The patient is skin type III. A clinical photograph showing a skin lesion. A male subject aged 34 — 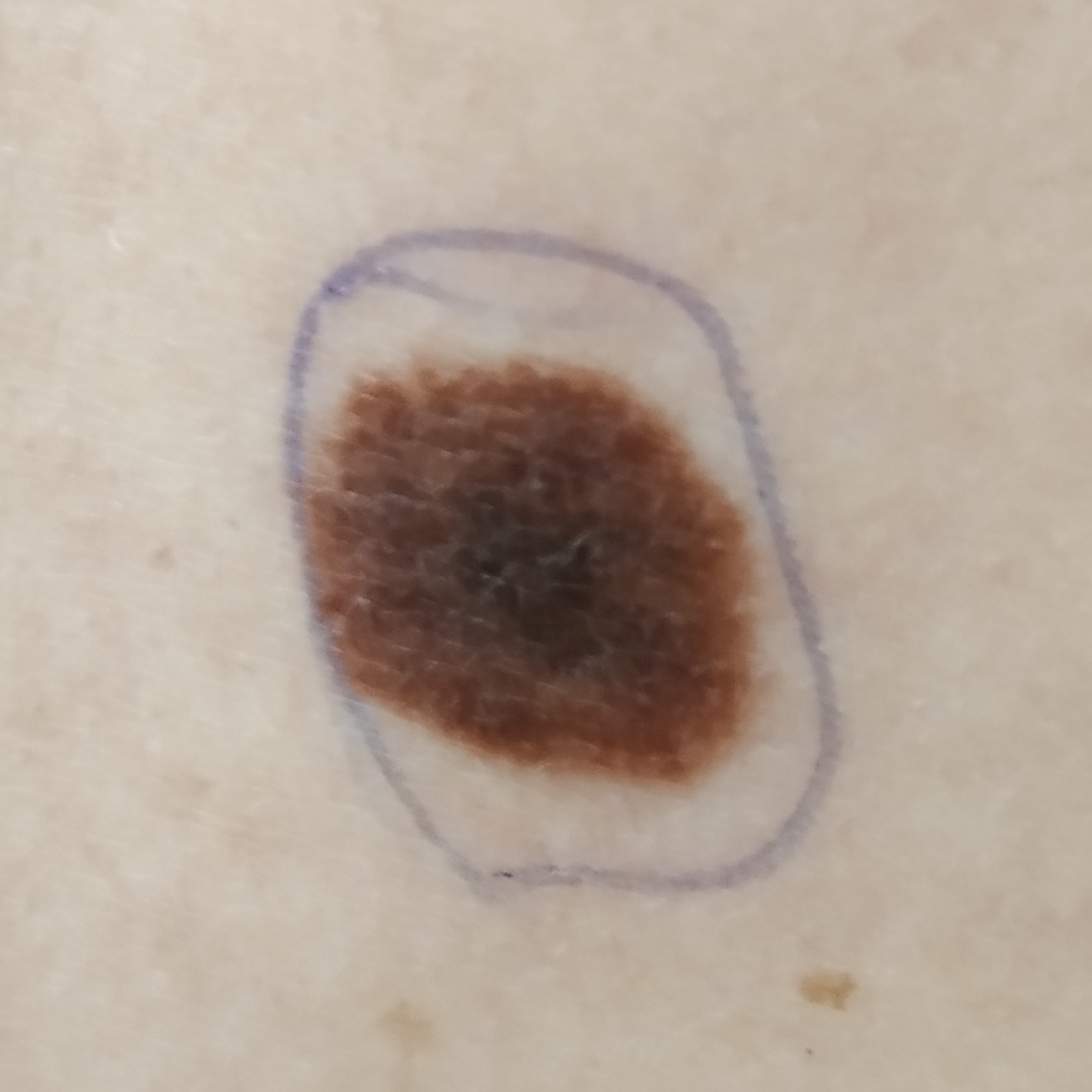Case:
- site · the back
- lesion size · approx. 15 × 12 mm
- symptoms · change in appearance
- impression · nevus (clinical consensus)